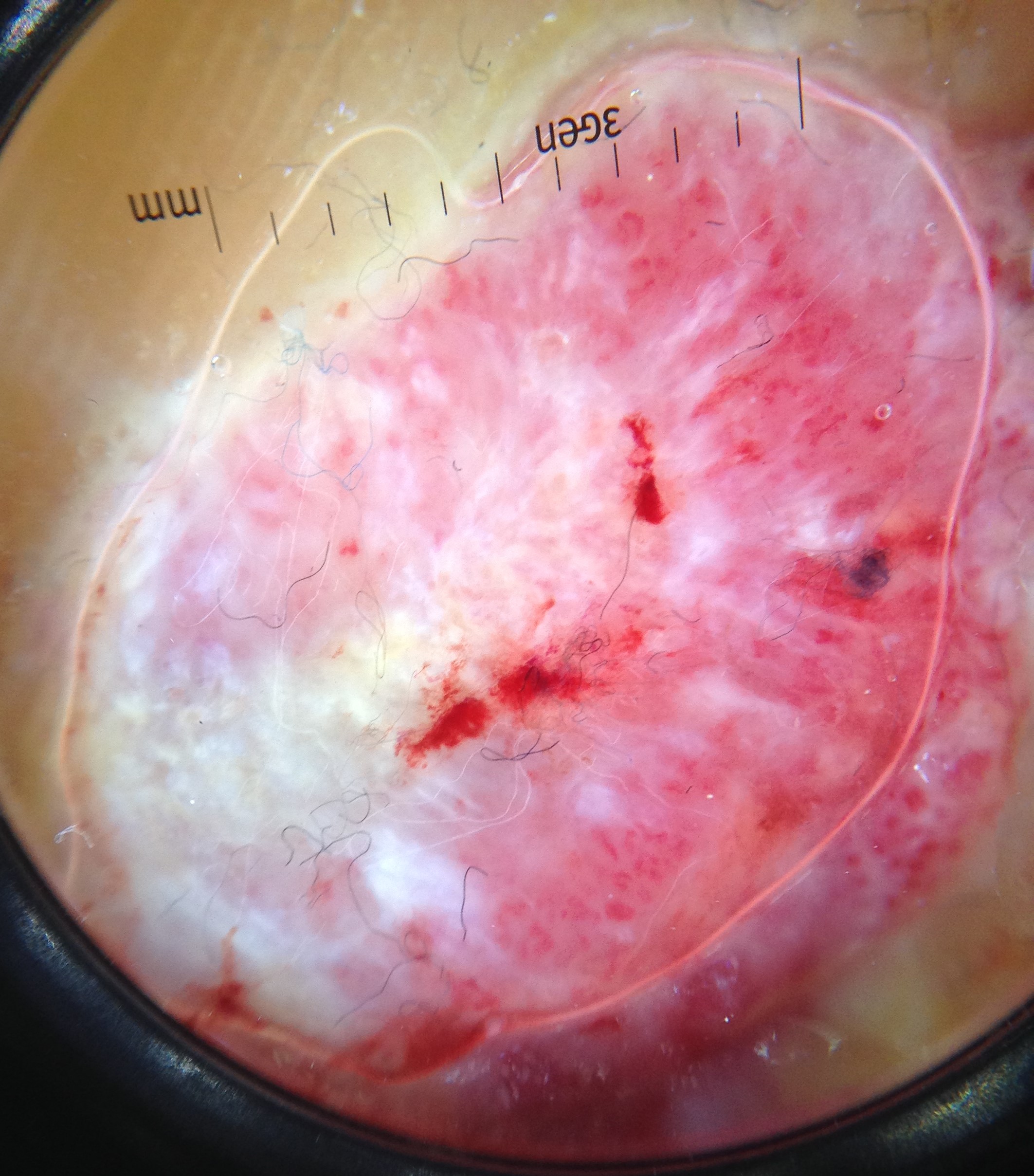A dermoscopic image of a skin lesion. The biopsy diagnosis was a skin cancer — an acral nodular melanoma.